A dermoscopic close-up of a skin lesion.
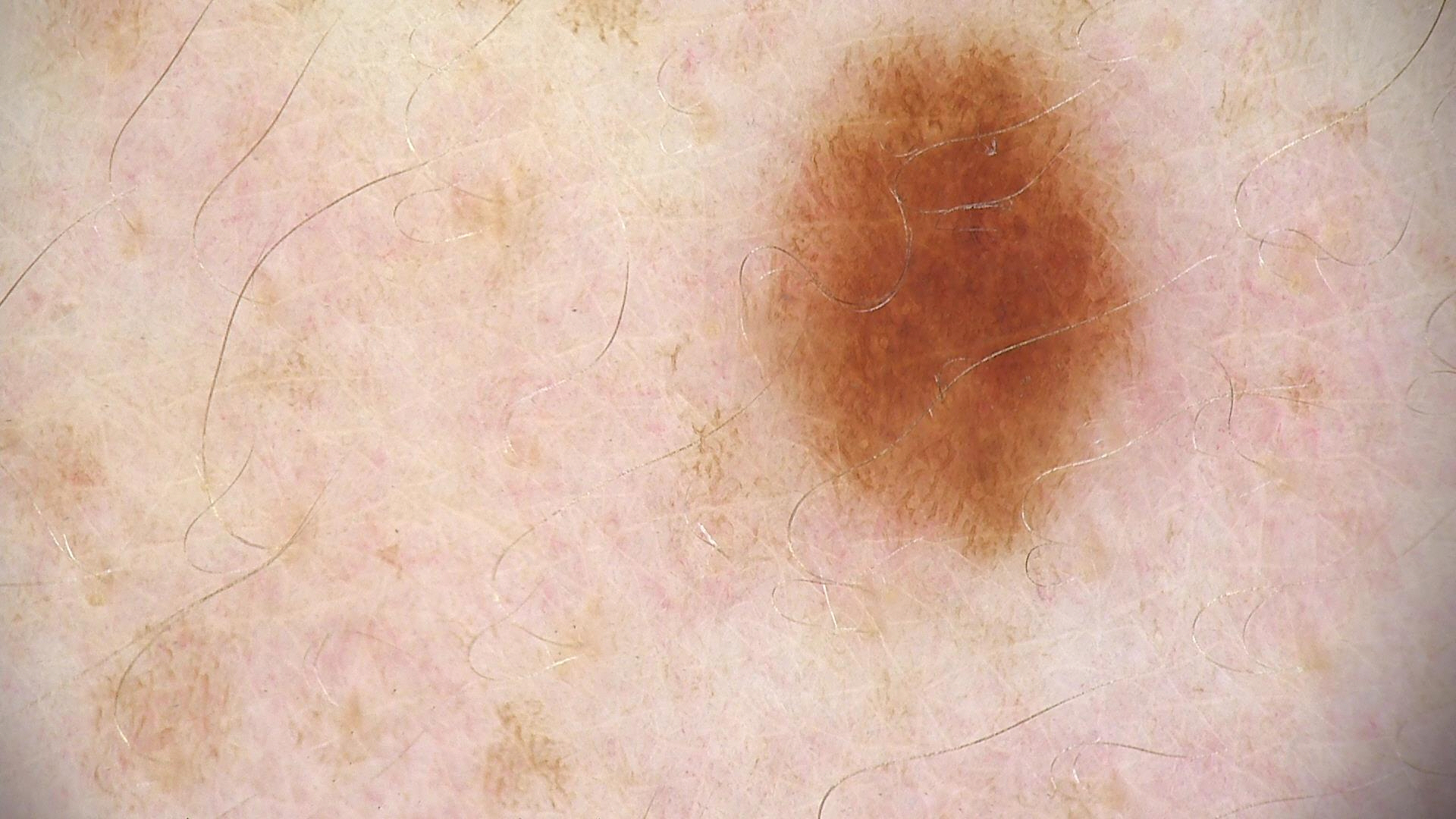diagnostic label: dysplastic junctional nevus (expert consensus).